A male patient approximately 85 years of age or older:
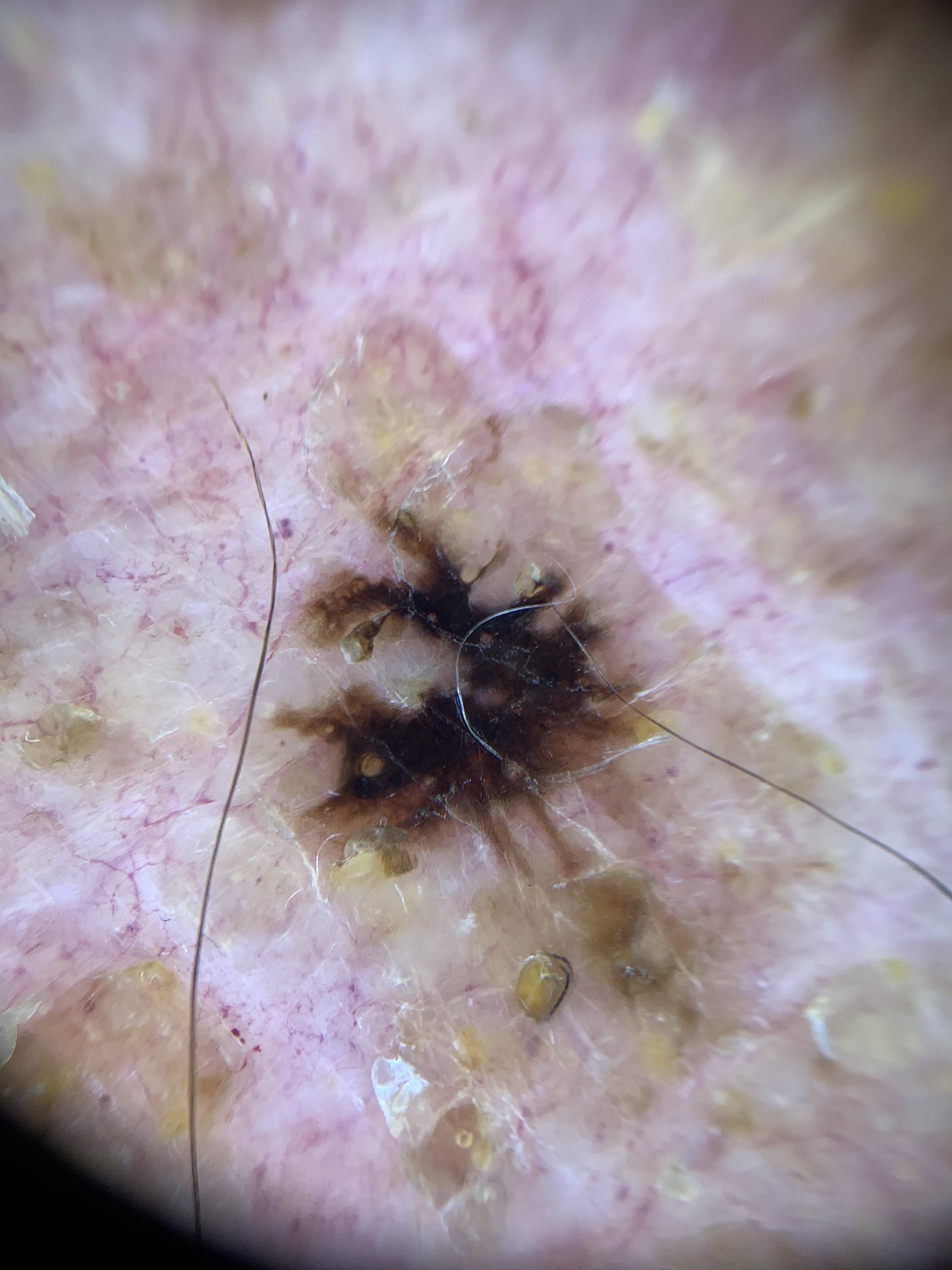Histopathologically confirmed as a benign, epidermal lesion — a seborrheic keratosis.